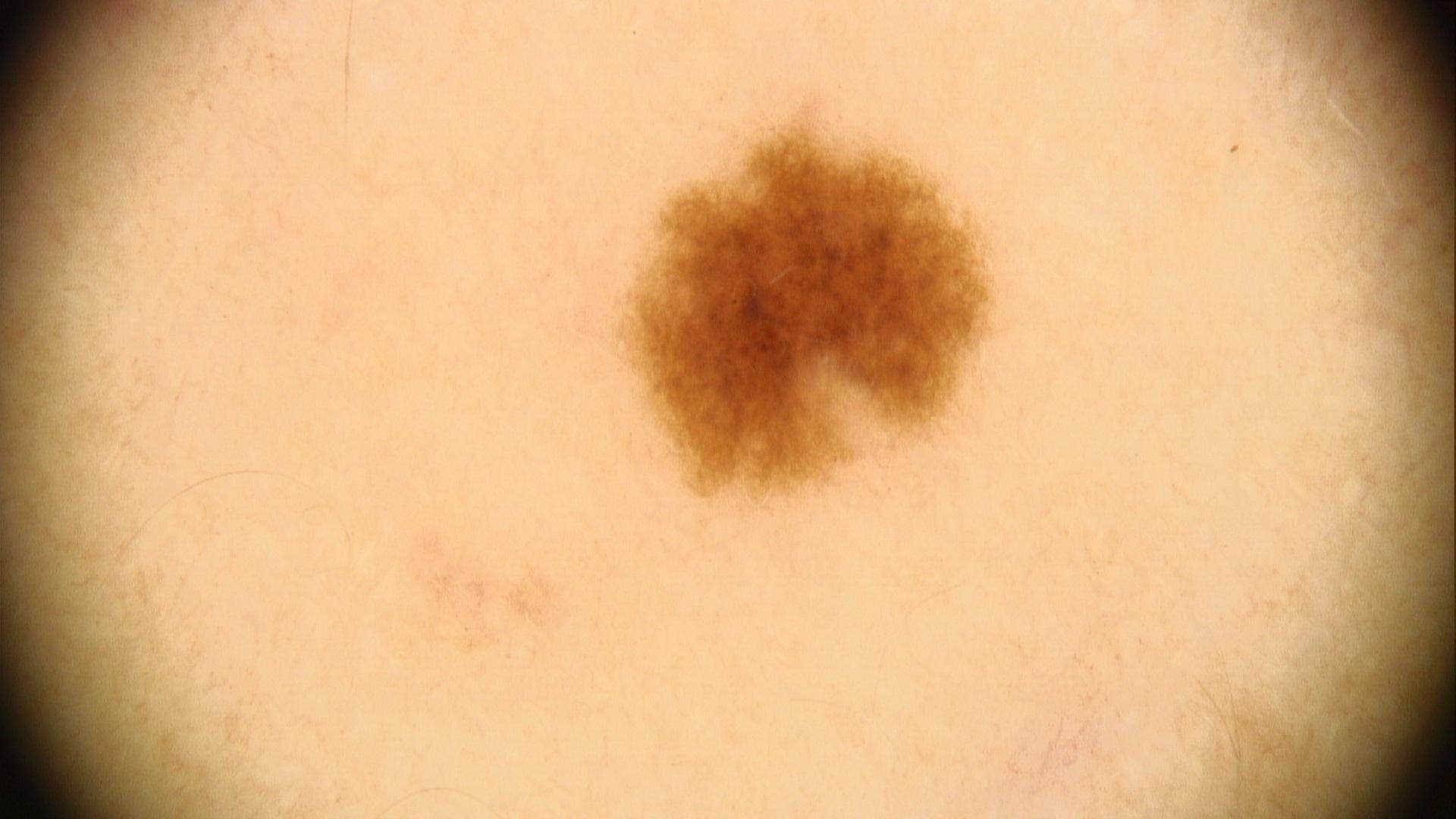Notes:
– assessment — Nevus